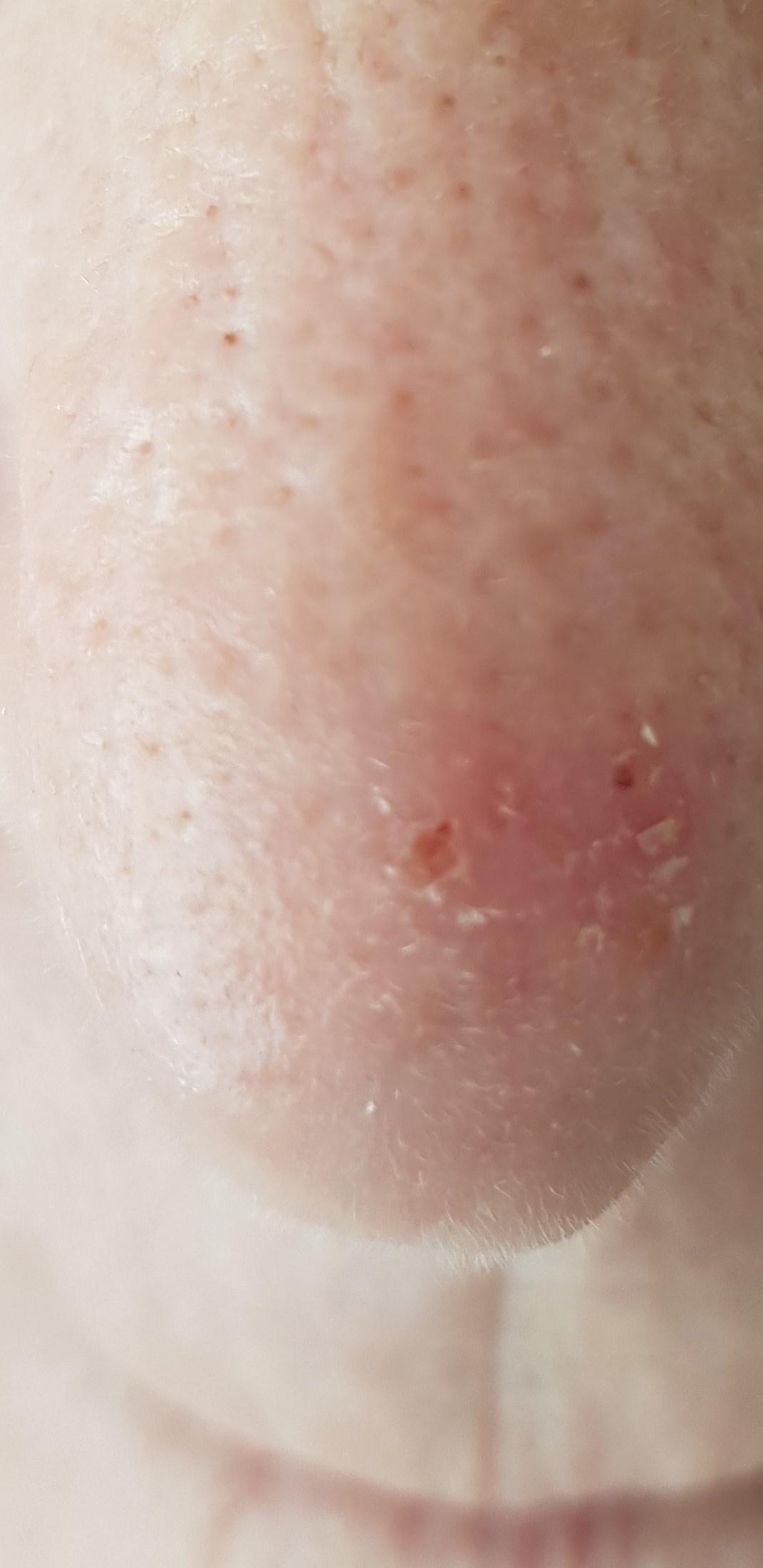A female patient aged approximately 75.
The lesion is located on the head or neck.
Biopsy-confirmed as a basal cell carcinoma.